The photo was captured at an angle: 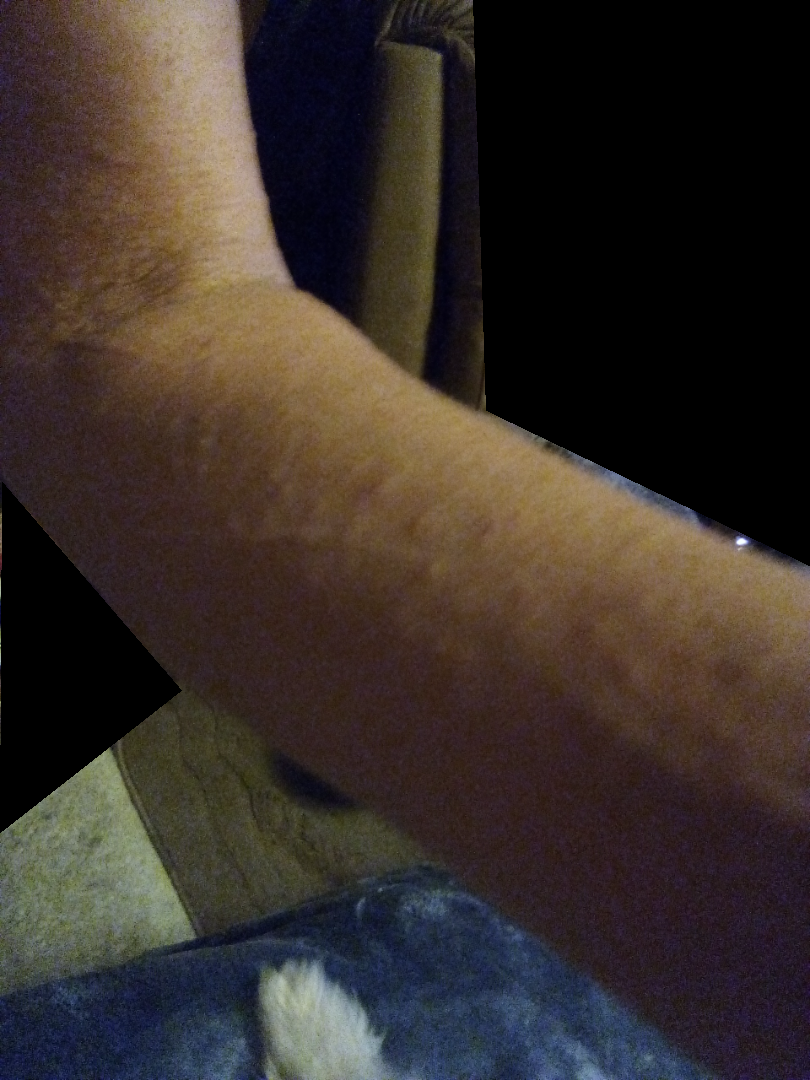Q: Fitzpatrick or Monk tone?
A: non-clinician graders estimated MST 3–4
Q: What is the differential diagnosis?
A: one reviewing dermatologist: Urticaria and Allergic Contact Dermatitis were considered with similar weight